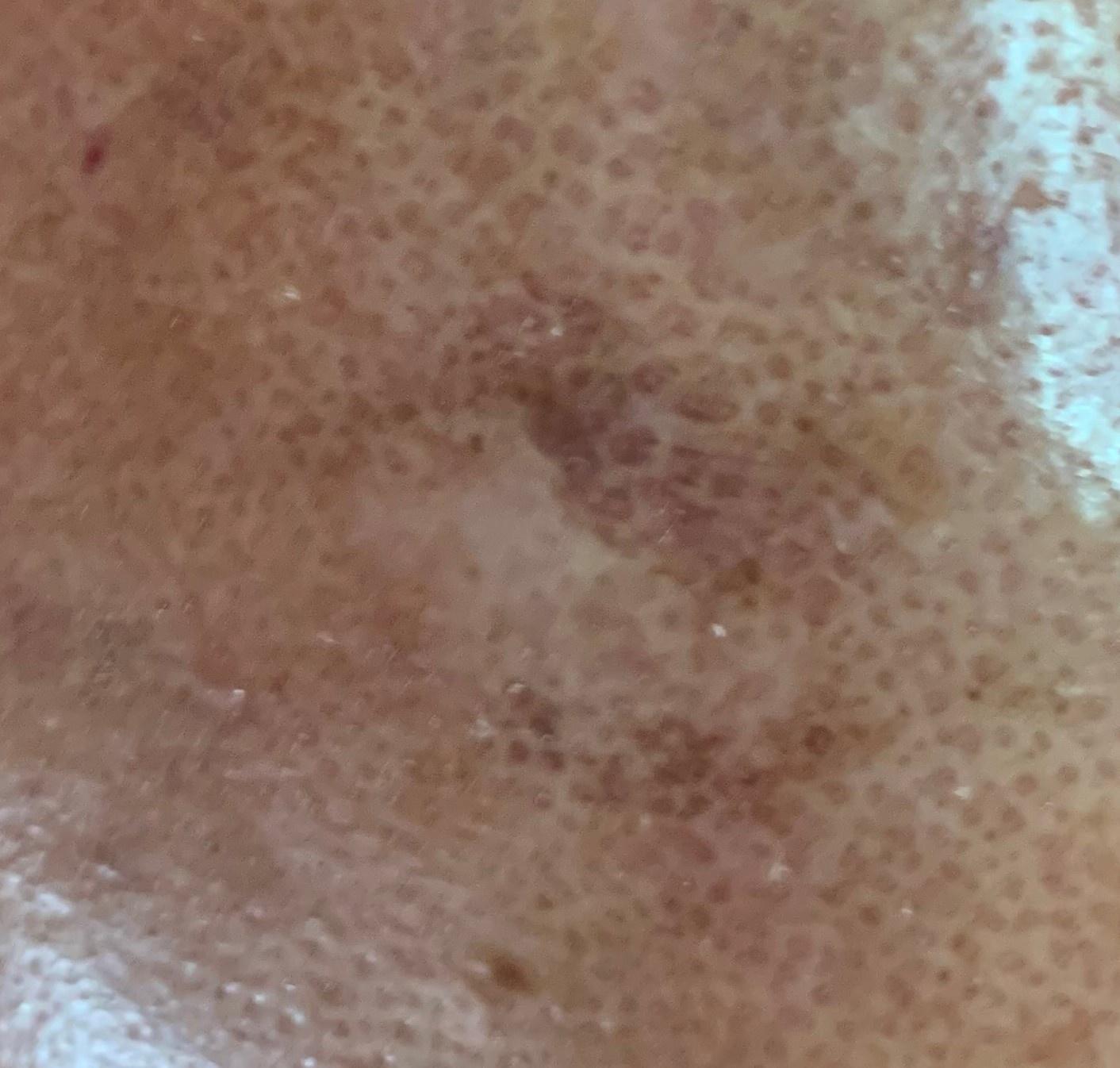Findings:
- diagnostic label: Solar or actinic keratosis (clinical impression)